The photo was captured at an angle; the contributor is 60–69, female; located on the front of the torso, head or neck and back of the torso.
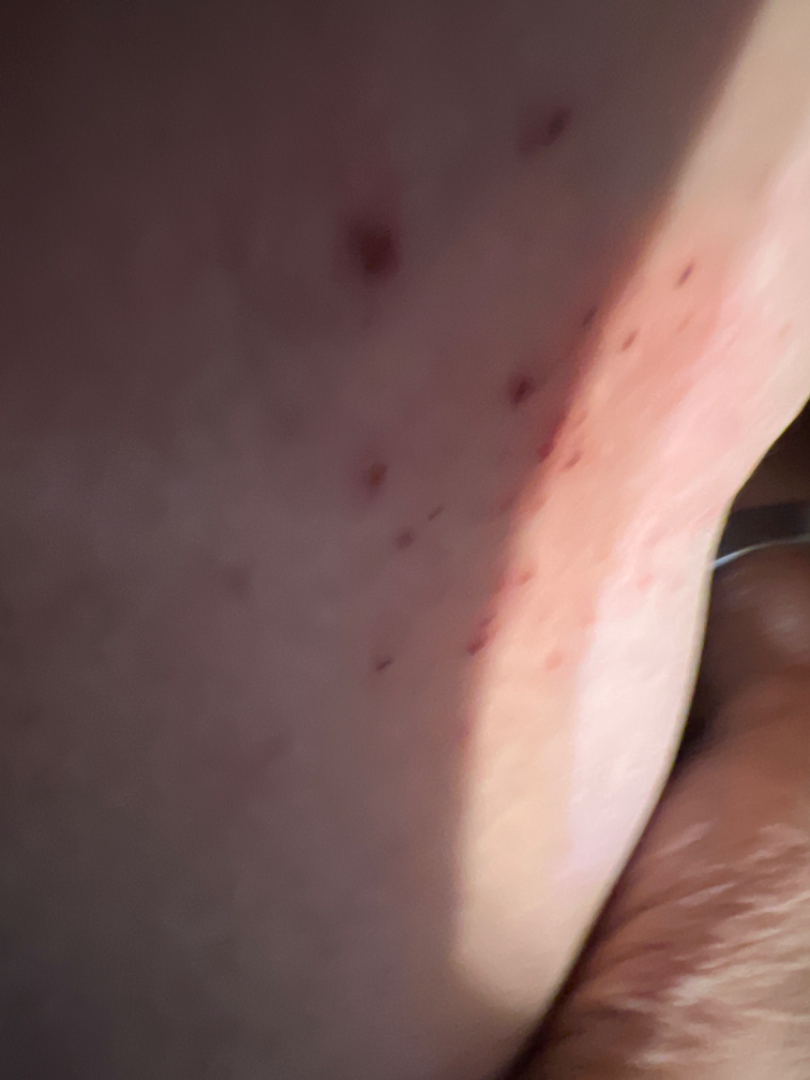| field | value |
|---|---|
| assessment | unable to determine |